A dermoscopic photograph of a skin lesion.
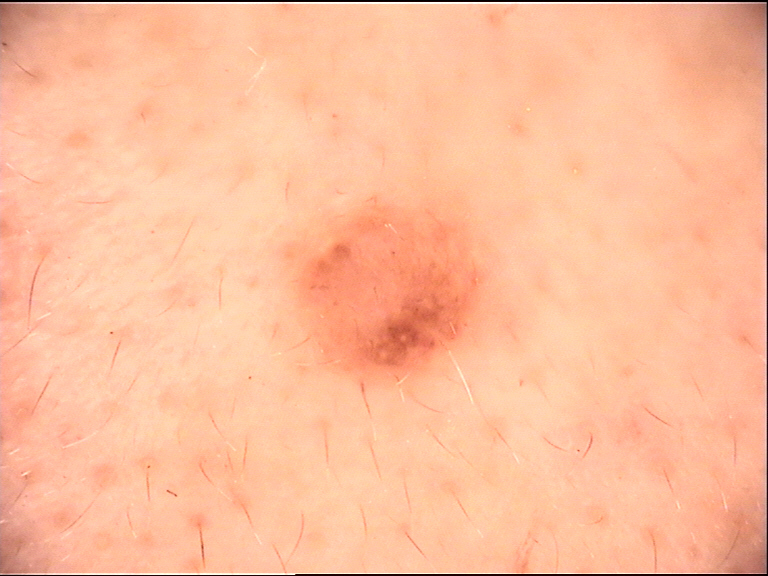<case>
  <lesion_type>
    <main_class>banal</main_class>
    <pattern>compound</pattern>
  </lesion_type>
  <diagnosis>
    <name>compound nevus</name>
    <code>cb</code>
    <malignancy>benign</malignancy>
    <super_class>melanocytic</super_class>
    <confirmation>expert consensus</confirmation>
  </diagnosis>
</case>